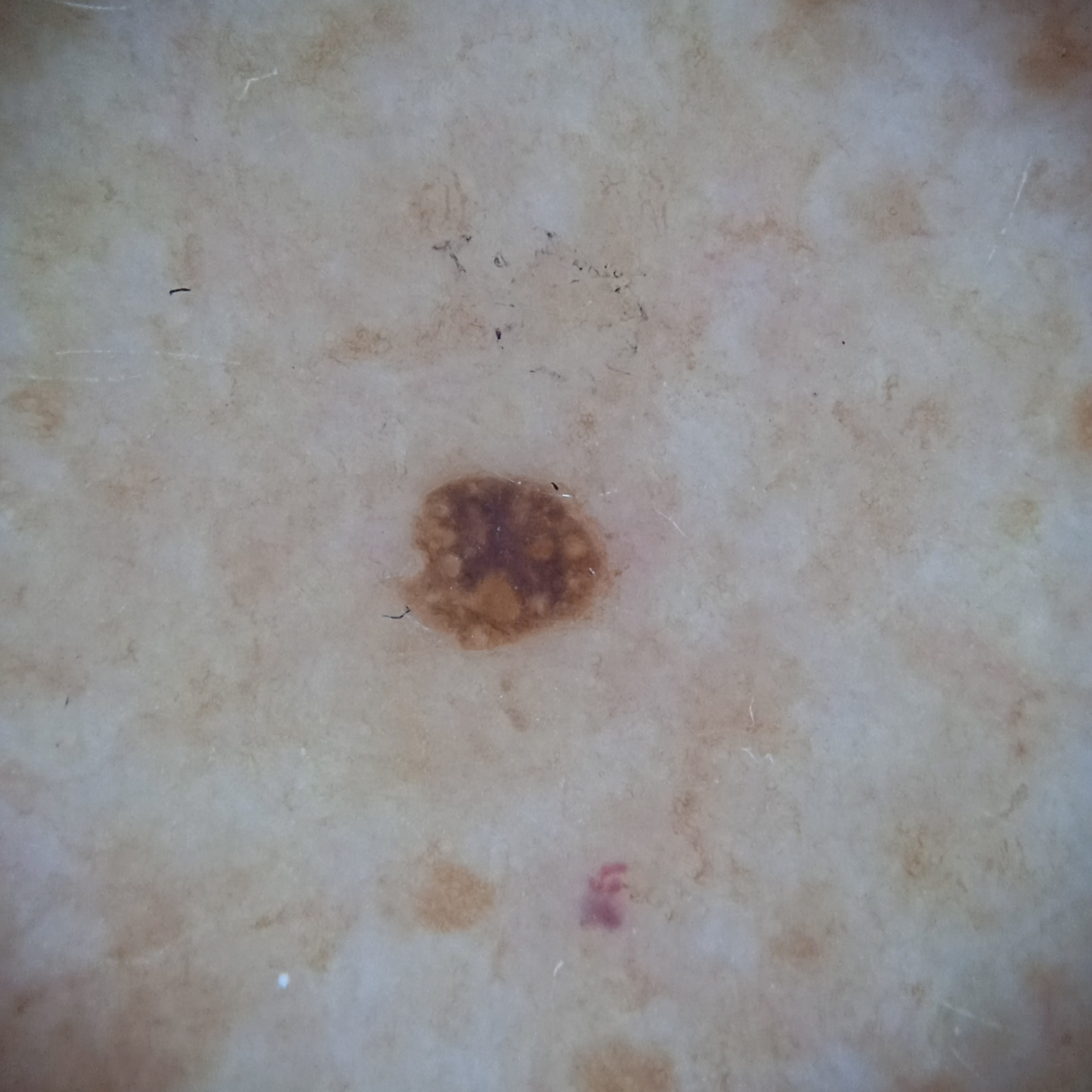Findings:
* assessment — seborrheic keratosis (dermatologist consensus)